A clinical photo of a skin lesion taken with a smartphone.
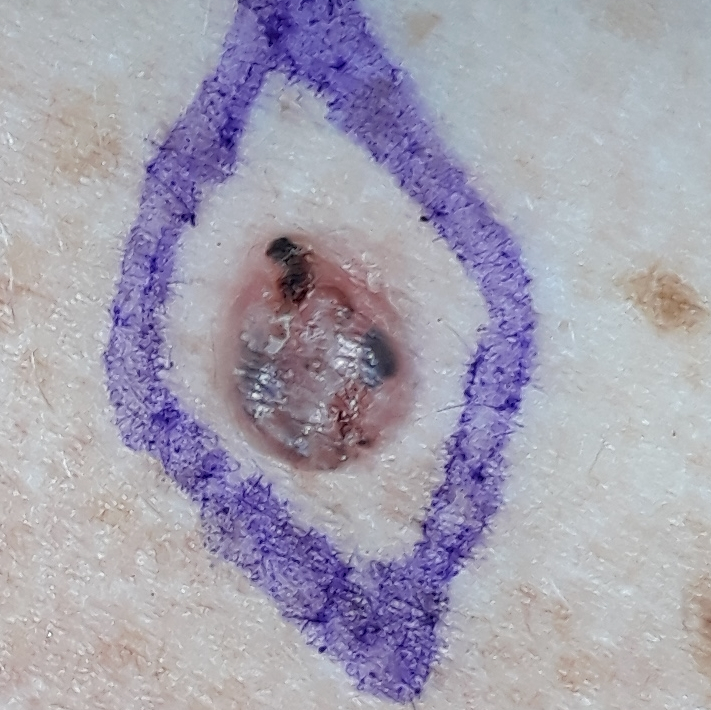{"lesion_location": "the chest", "diagnosis": {"name": "basal cell carcinoma", "code": "BCC", "malignancy": "malignant", "confirmation": "histopathology"}}